A female subject, aged 58-62. A dermatoscopic image of a skin lesion:
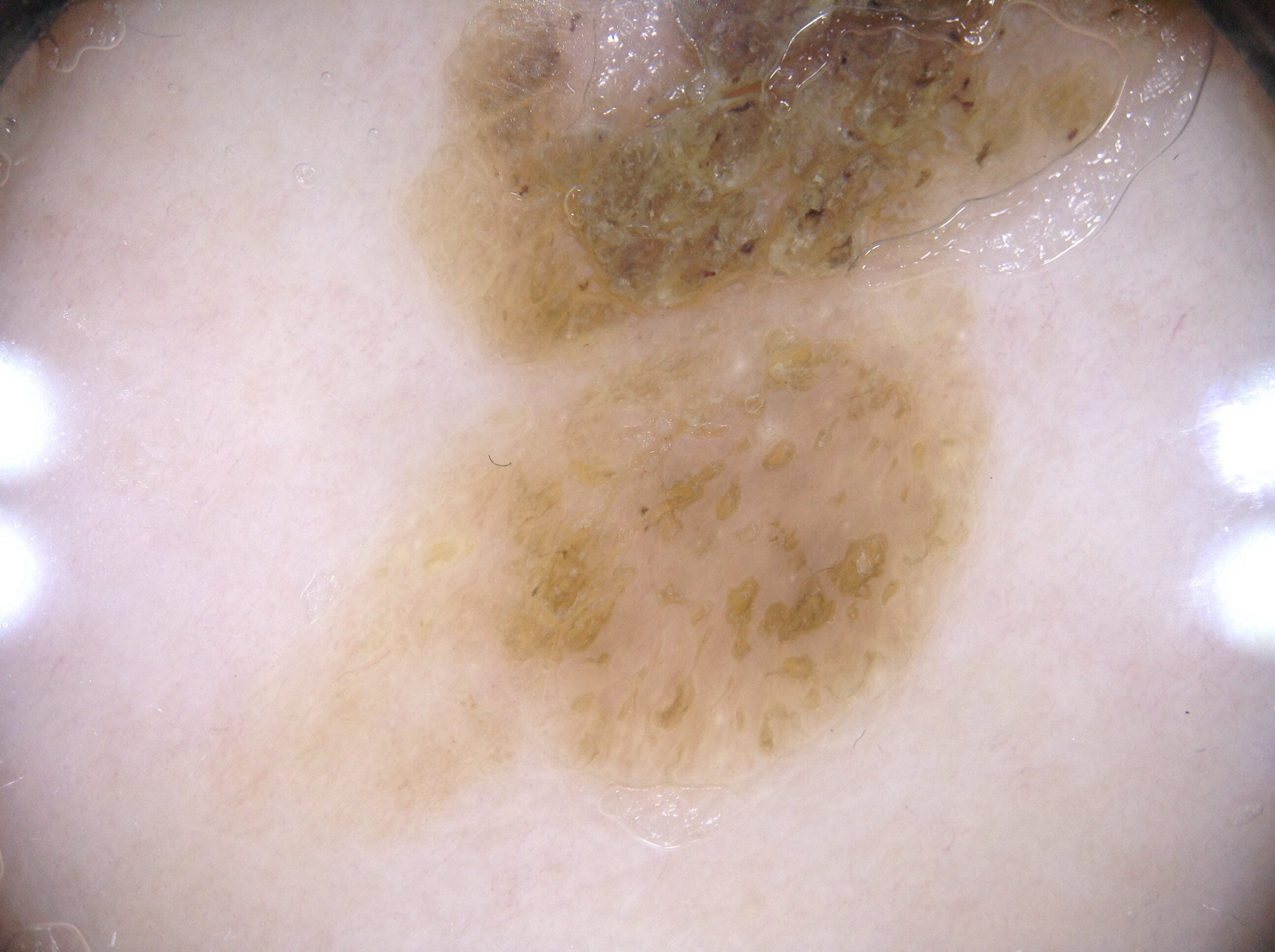The lesion is located at x1=190 y1=2 x2=1188 y2=898. The lesion covers approximately 43% of the dermoscopic field. Dermoscopic review identifies milia-like cysts. Consistent with a seborrheic keratosis, a benign skin lesion.